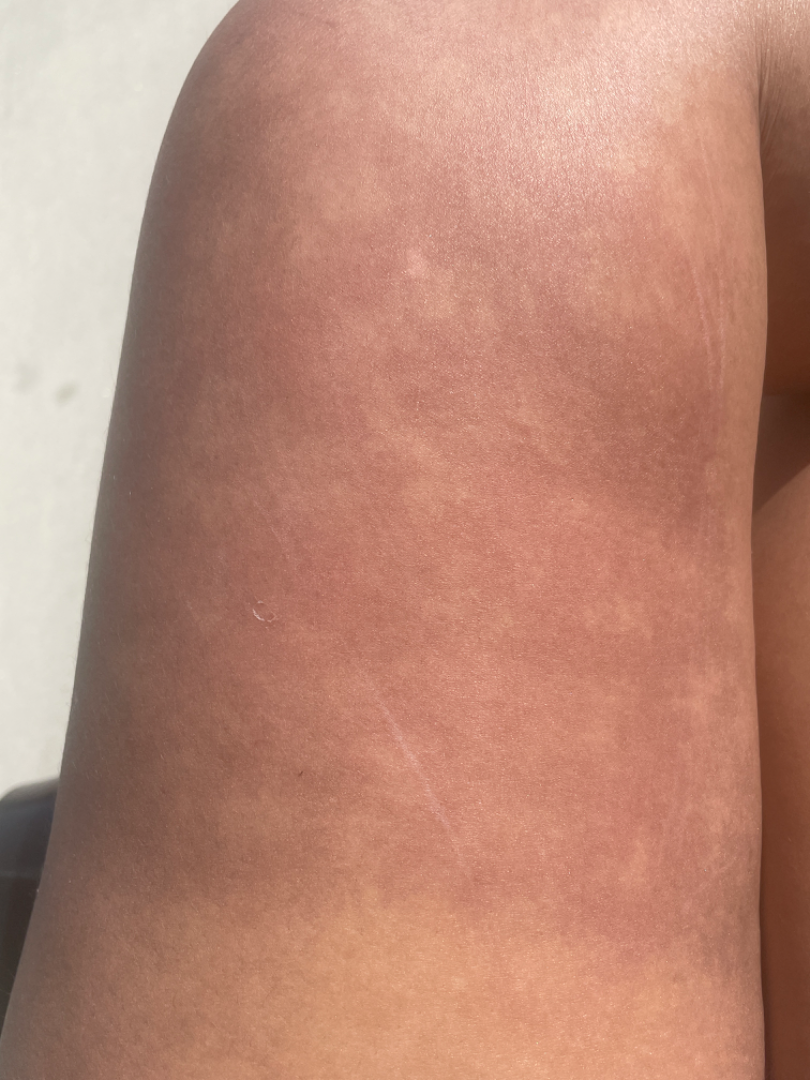{
  "body_site": "leg",
  "shot_type": "close-up",
  "texture": "flat",
  "duration": "about one day",
  "skin_tone": {
    "fitzpatrick": "IV"
  },
  "symptoms": "burning",
  "differential": {
    "Post-Inflammatory hyperpigmentation": 0.55,
    "Erythema ab igne": 0.27,
    "Erythema dyschromicum perstans": 0.18
  }
}